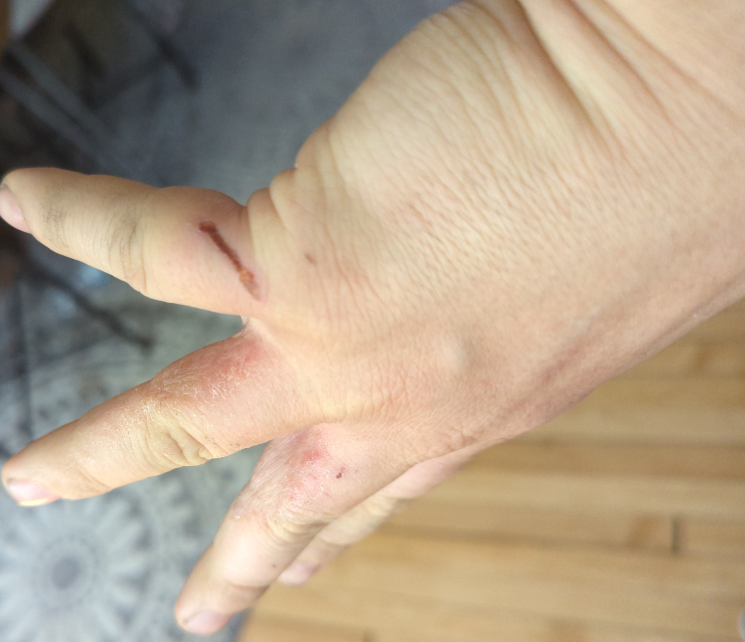Q: Could the case be diagnosed?
A: could not be assessed
Q: Any systemic symptoms?
A: none reported
Q: What symptoms does the patient report?
A: bothersome appearance, darkening, itching and pain
Q: What is the affected area?
A: back of the hand
Q: How was the photo taken?
A: at a distance
Q: What is the lesion texture?
A: raised or bumpy and rough or flaky